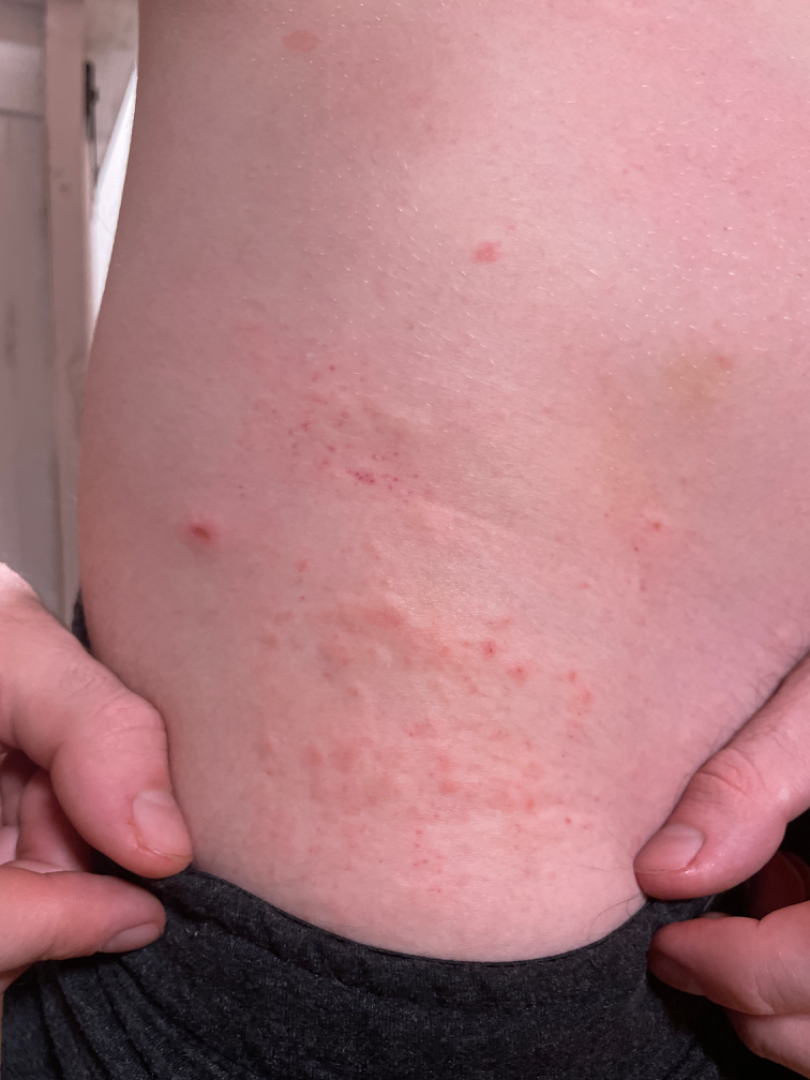body site: front of the torso | framing: close-up | present for: less than one week | assessment: favoring Allergic Contact Dermatitis; also on the differential is Urticaria; a remote consideration is Eczema.